The lesion involves the head or neck, front of the torso, arm and back of the torso. The condition has been present for less than one week. The contributor notes enlargement, bothersome appearance and itching. Self-reported Fitzpatrick IV; human graders estimated 3 on the Monk skin tone scale. The lesion is described as raised or bumpy and rough or flaky. Female subject, age 18–29. An image taken at an angle. Self-categorized by the patient as a rash.
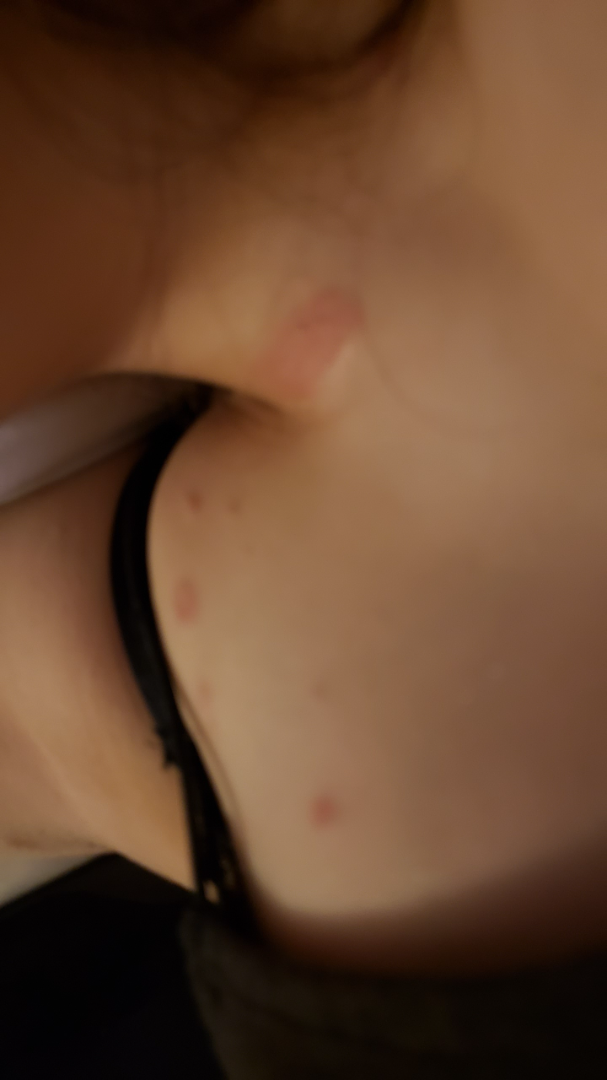Findings: The dermatologist could not determine a likely condition from the photograph alone.